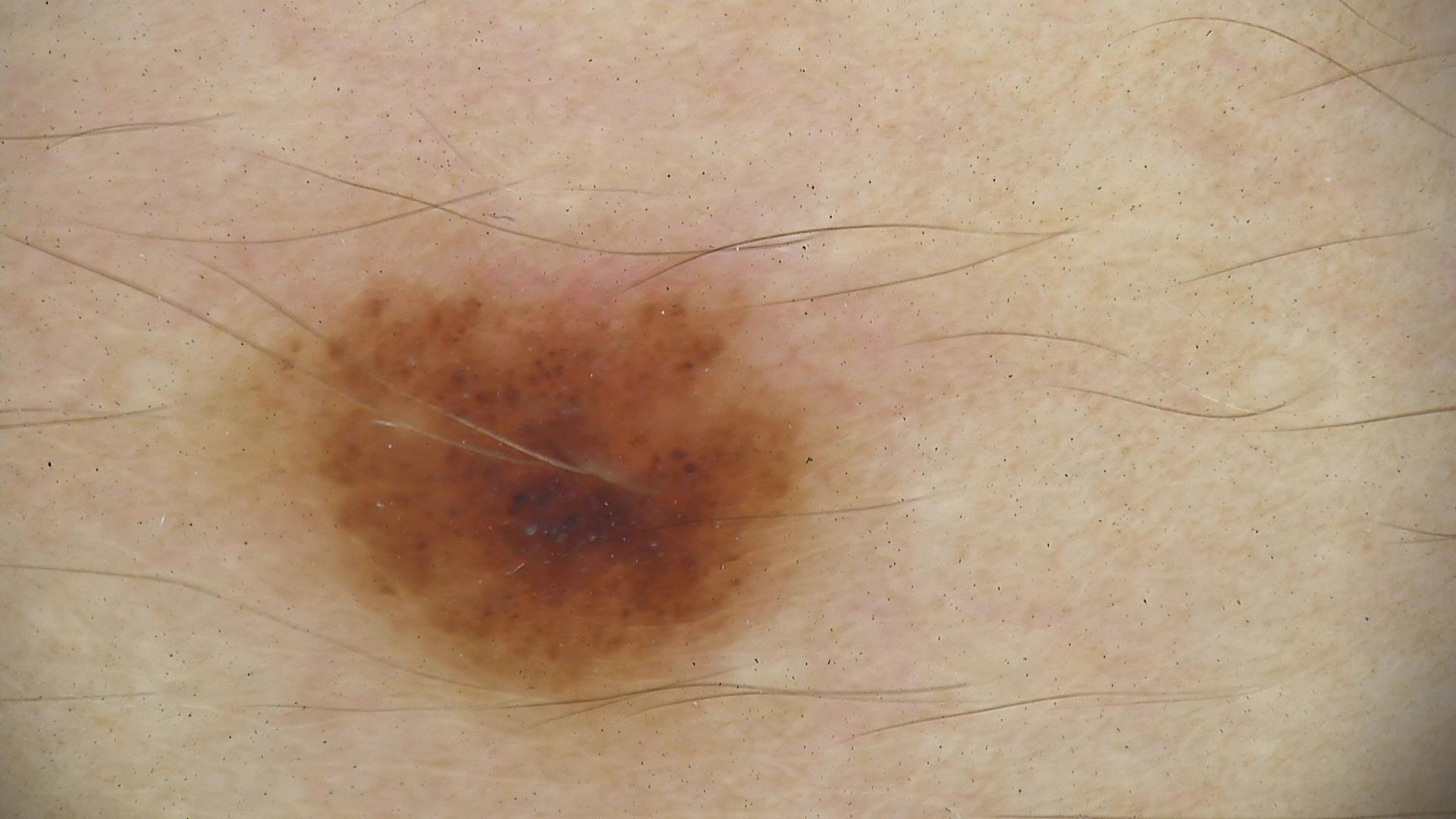A dermoscopic photograph of a skin lesion.
Classified as a benign lesion — a dysplastic junctional nevus.